The patient was assessed as Fitzpatrick skin type III; a male patient 57 years of age:
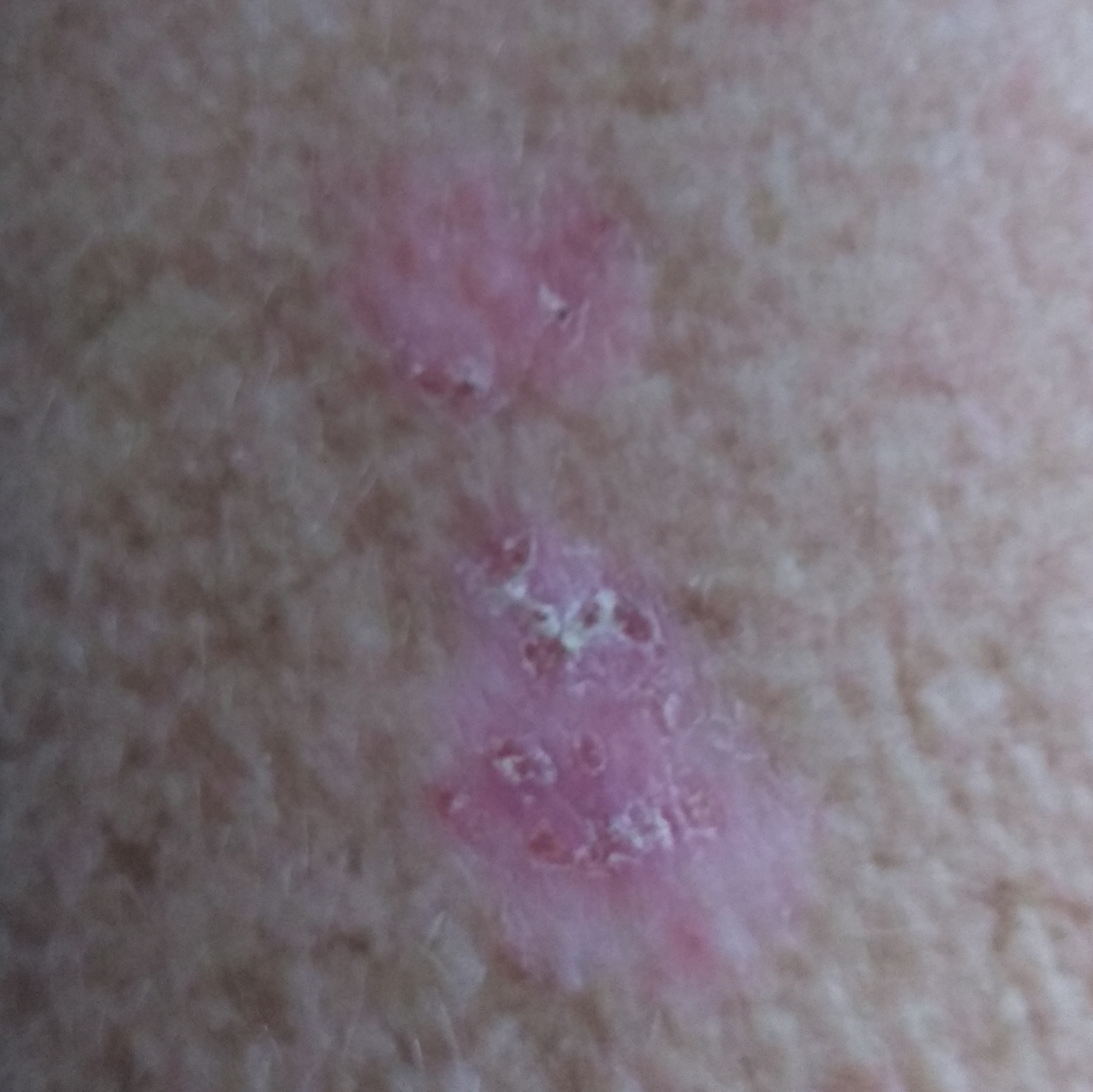Case:
- location · an arm
- diameter · 20x8 mm
- diagnostic label · basal cell carcinoma (biopsy-proven)